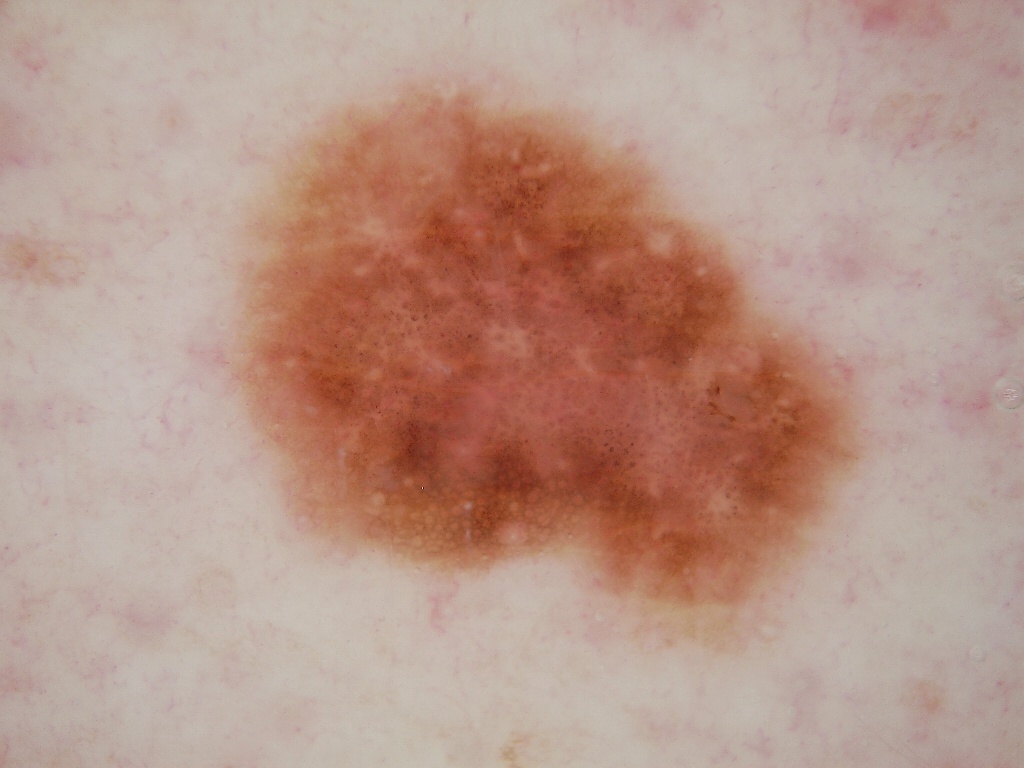Q: What kind of image is this?
A: dermatoscopic image of a skin lesion
Q: What dermoscopic features are present?
A: pigment network, milia-like cysts, globules, and negative network
Q: What is the lesion's bounding box?
A: 215/72/883/656
Q: What is this lesion?
A: a melanoma, a skin cancer